A dermoscopic image of a skin lesion: 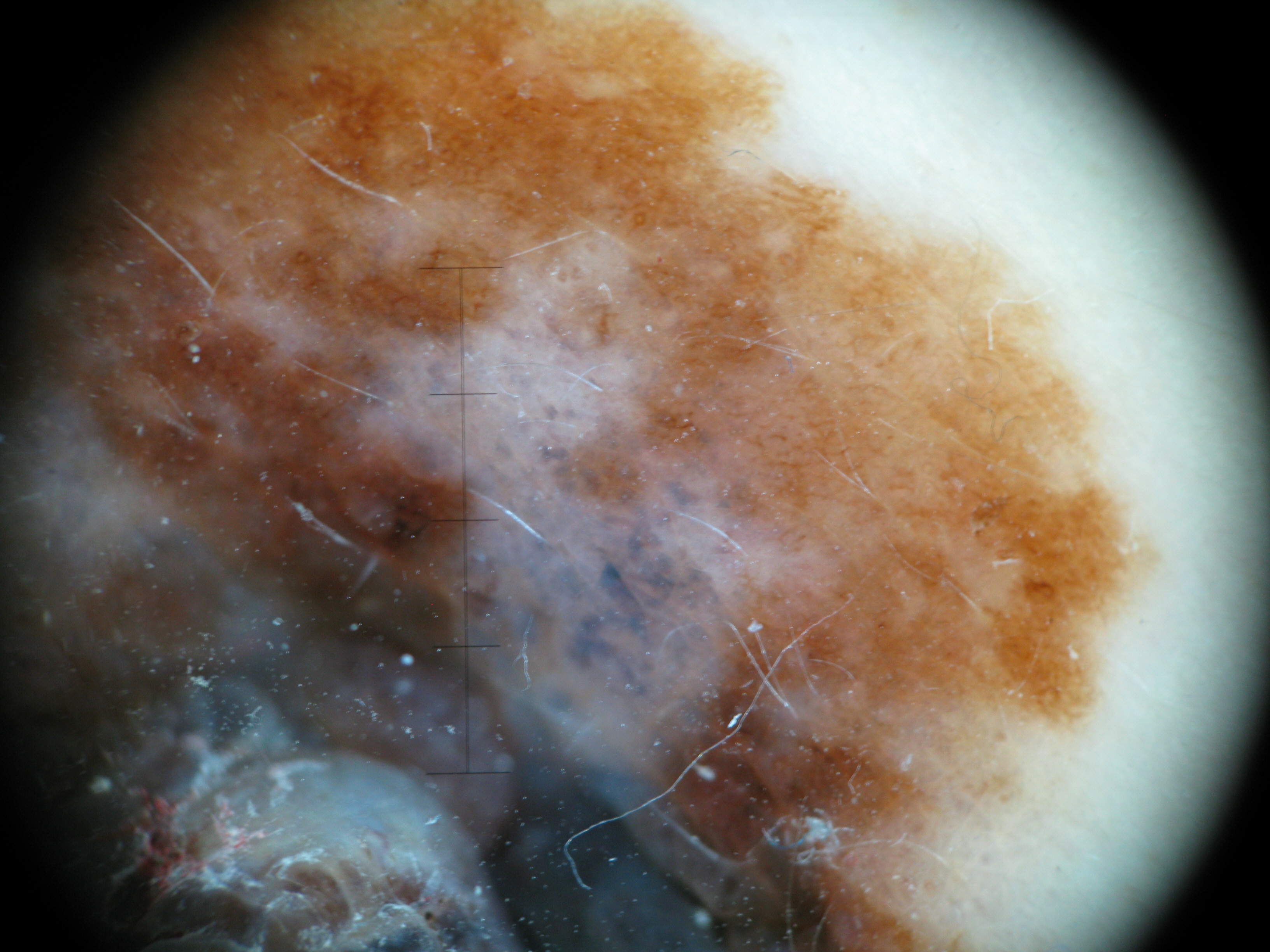label: melanoma (biopsy-proven).